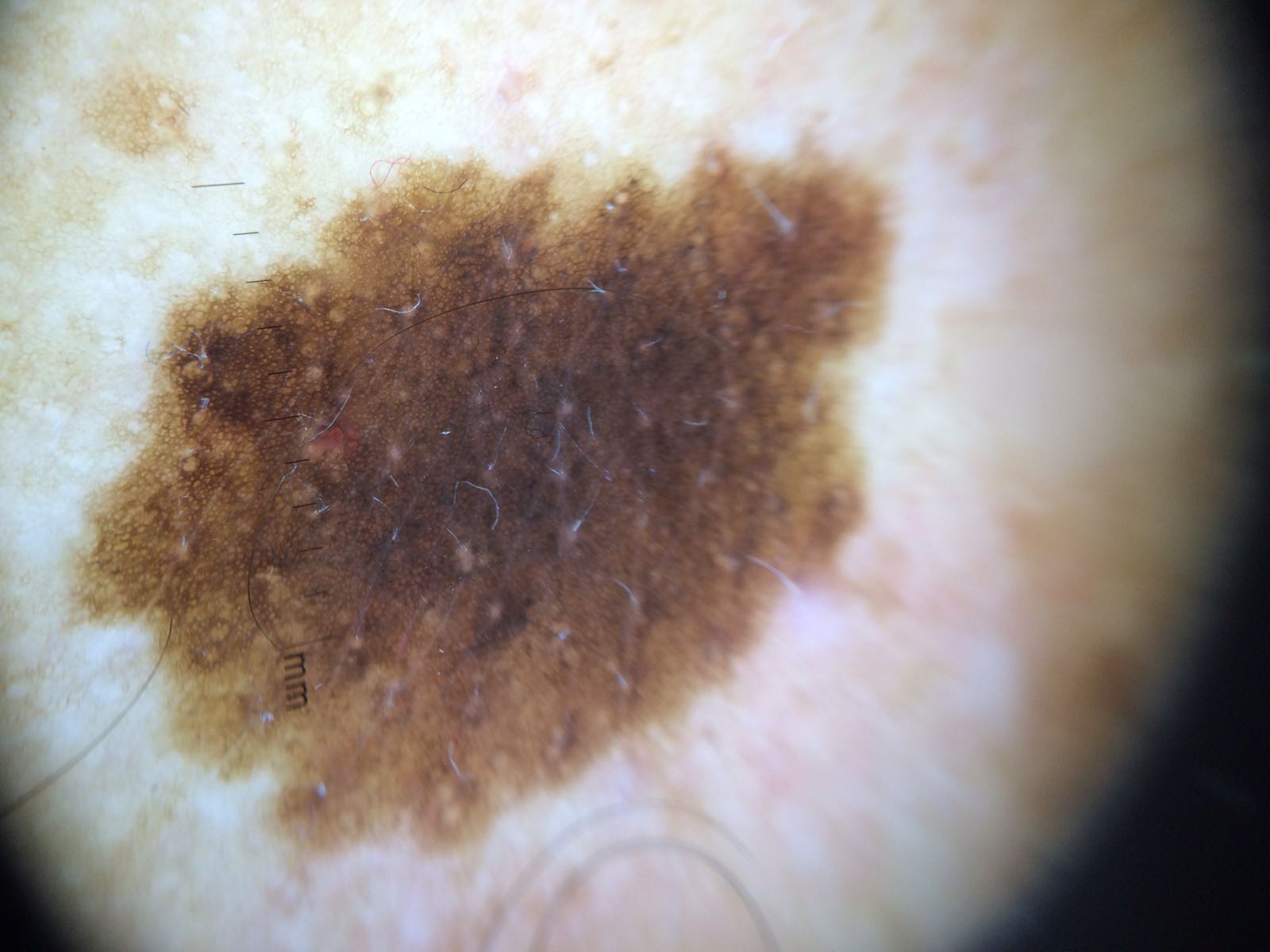{
  "image": "dermoscopy",
  "lesion_type": {
    "main_class": "banal",
    "pattern": "compound"
  },
  "diagnosis": {
    "name": "congenital compound nevus",
    "code": "ccb",
    "malignancy": "benign",
    "super_class": "melanocytic",
    "confirmation": "expert consensus"
  }
}